Located on the arm · the subject is female · an image taken at a distance:
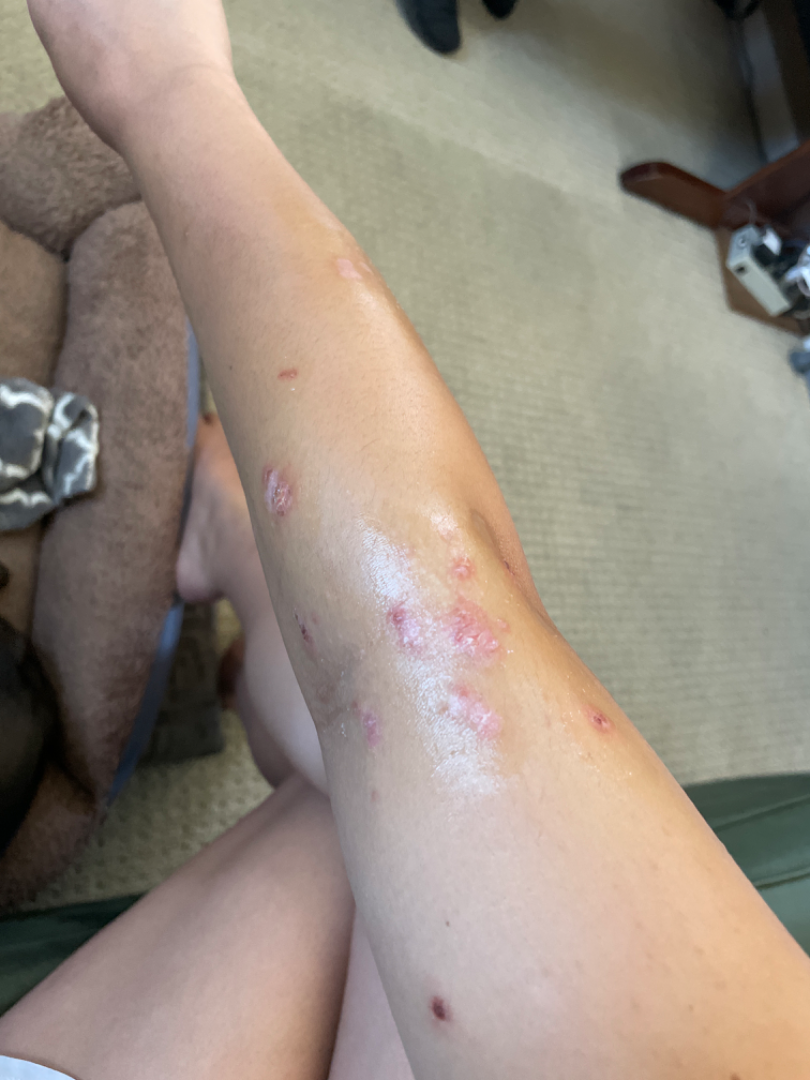diagnostic considerations: most consistent with Lichen Simplex Chronicus; possibly Inflicted skin lesions; an alternative is Eczema; less likely is Infected eczema; lower on the differential is Abrasion of wrist